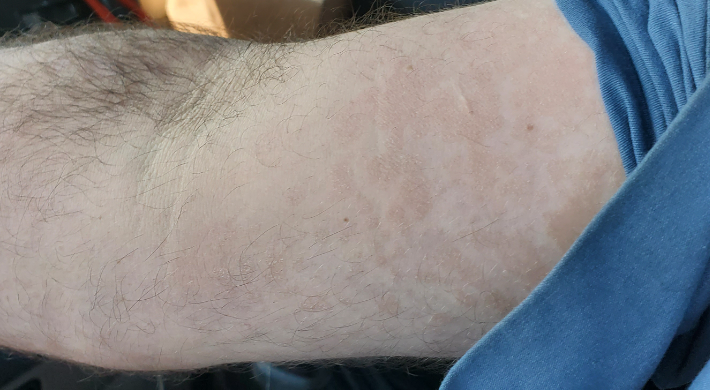The reviewer was unable to grade this case for skin condition.